A dermoscopic close-up of a skin lesion:
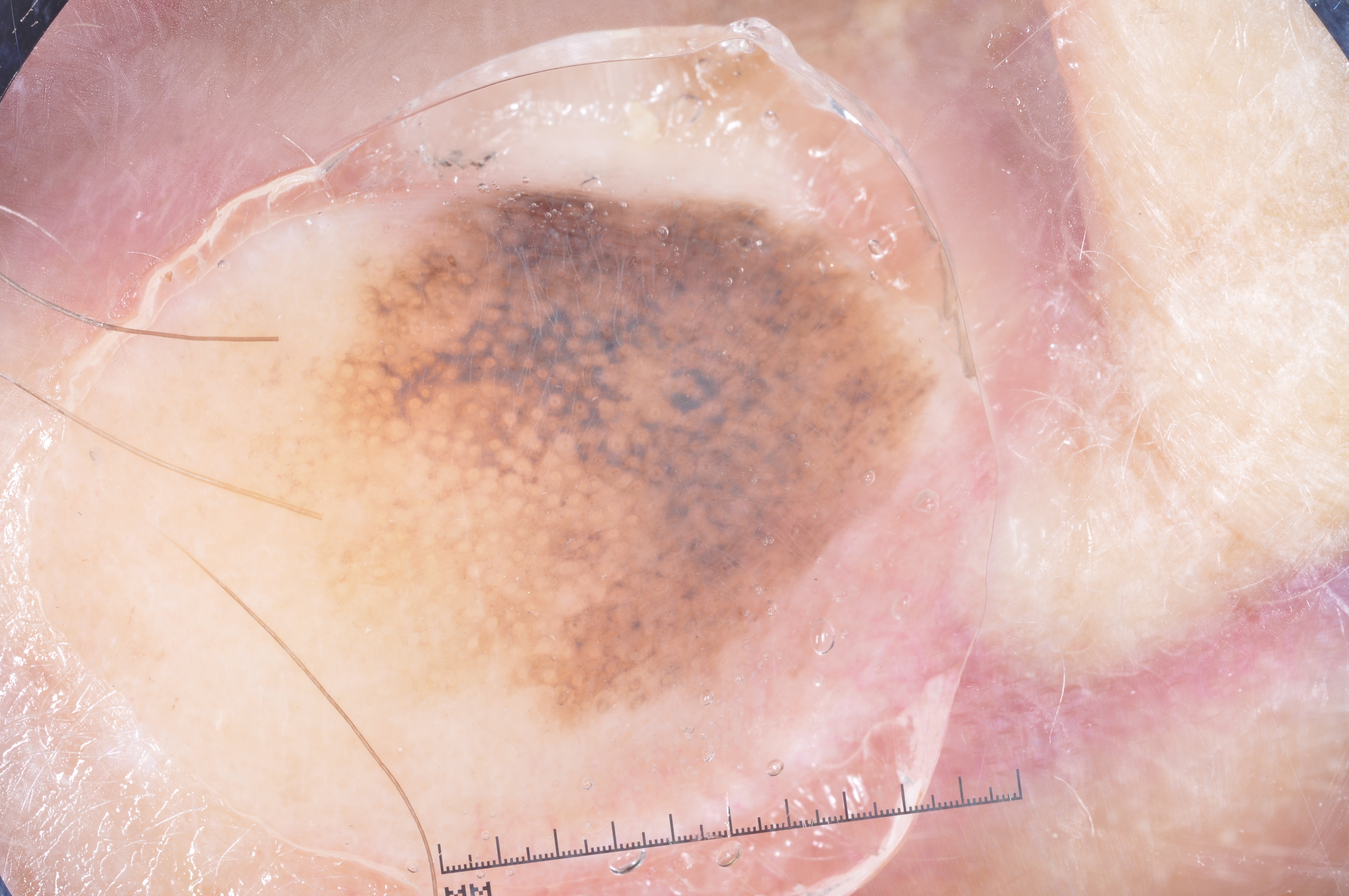Image and clinical context: With coordinates (x1, y1, x2, y2), lesion location: (219, 179, 953, 739). Diagnosis: Confirmed on histopathology as a melanoma, a malignant skin lesion.